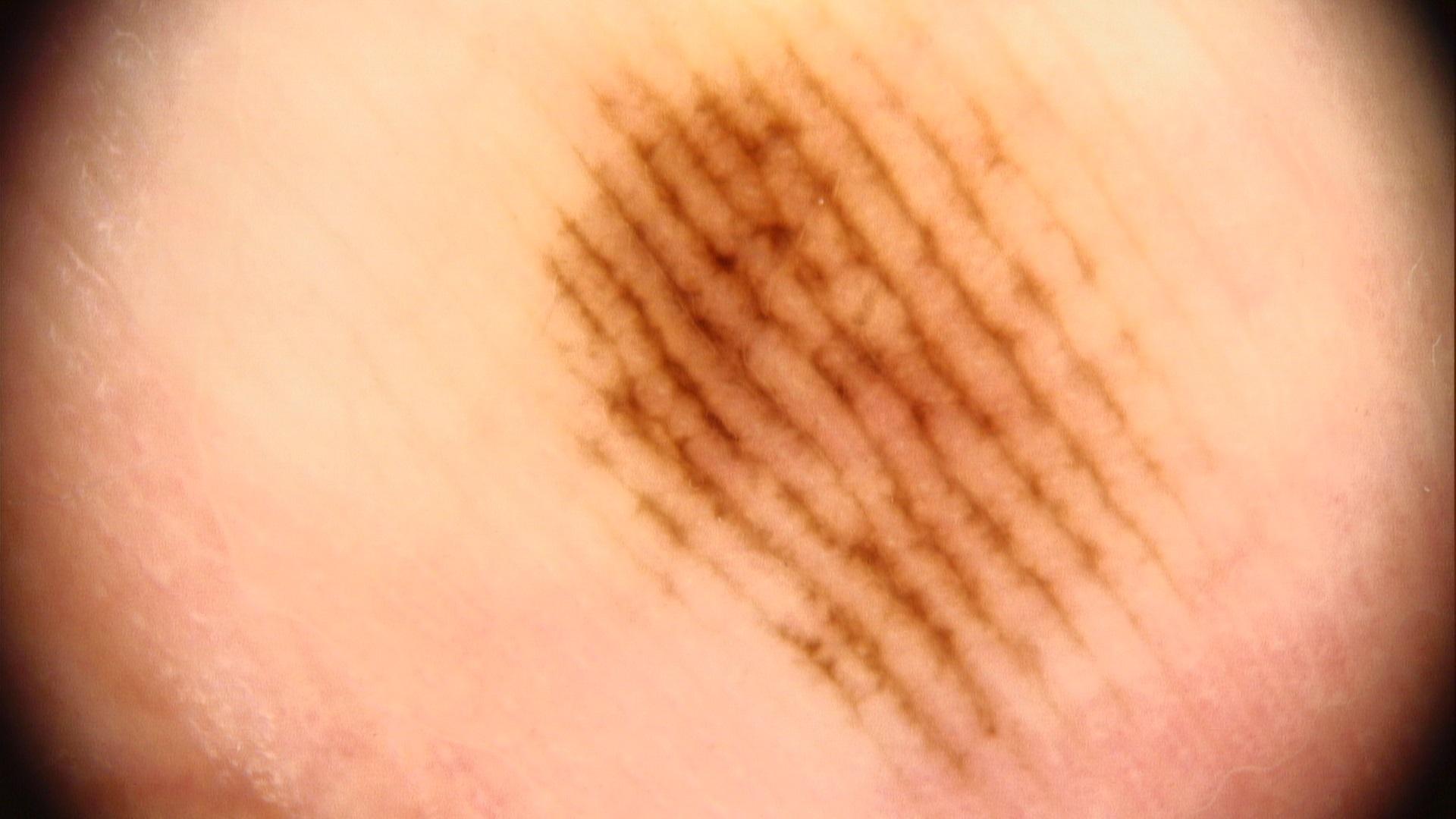| field | value |
|---|---|
| image | dermoscopic image |
| Fitzpatrick | III |
| subject | male, in their 60s |
| impression | Nevus |